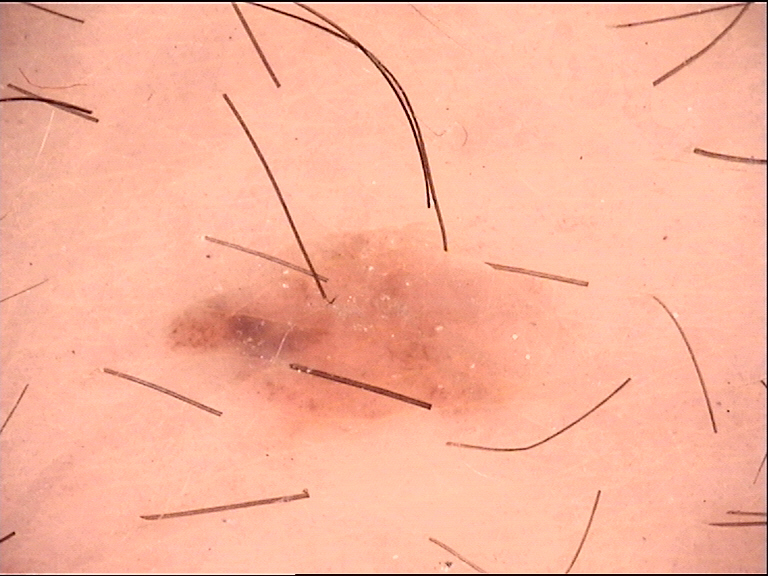diagnosis: dysplastic junctional nevus (expert consensus).